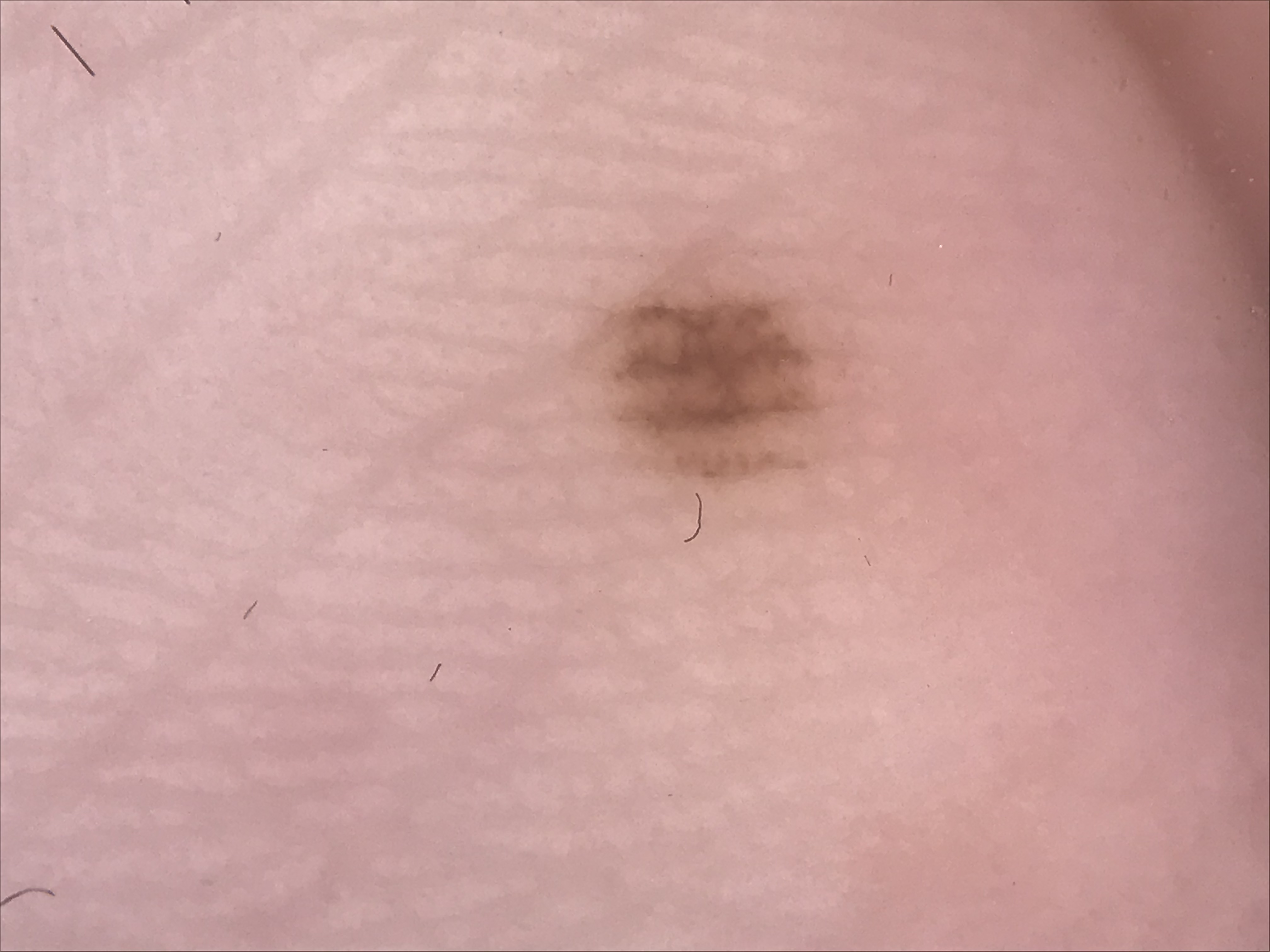Q: What kind of image is this?
A: dermoscopy
Q: What is the diagnosis?
A: acral junctional nevus (expert consensus)